The patient notes the condition has been present for three to twelve months · the patient is 50–59, female · texture is reported as rough or flaky and raised or bumpy · the patient notes itching, enlargement and bothersome appearance · a close-up photograph · the affected area is the head or neck · no constitutional symptoms were reported.
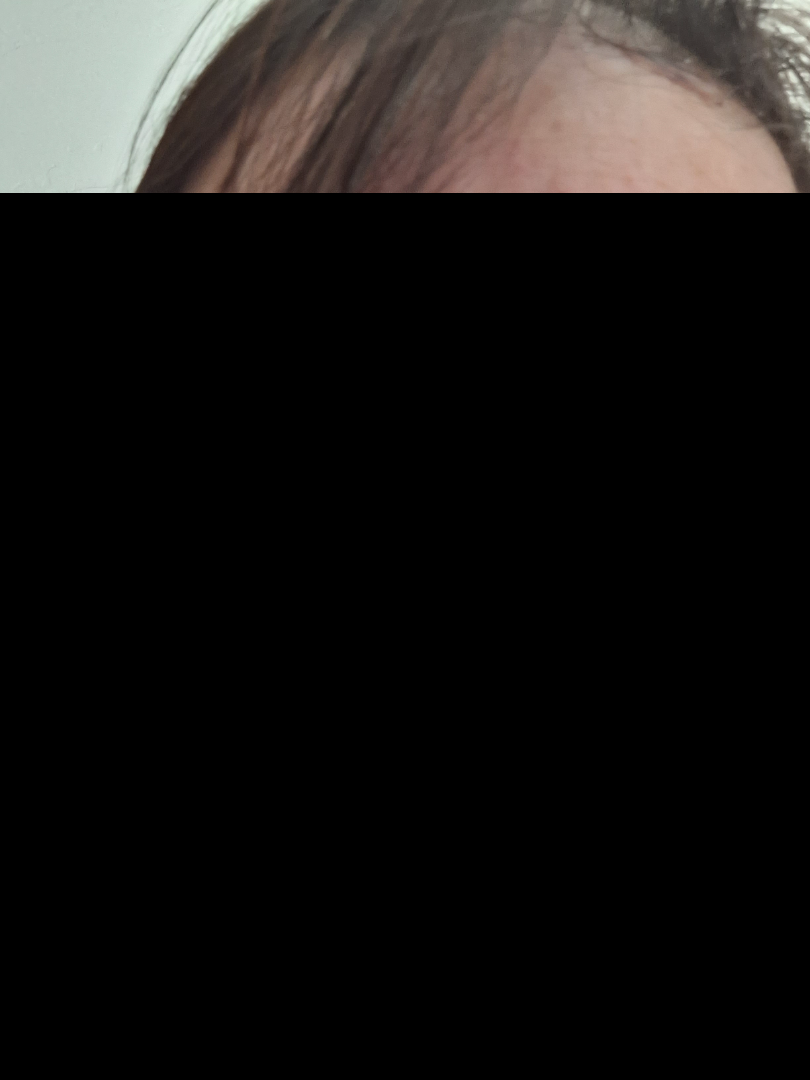Notes:
• assessment — Rosacea (100%)